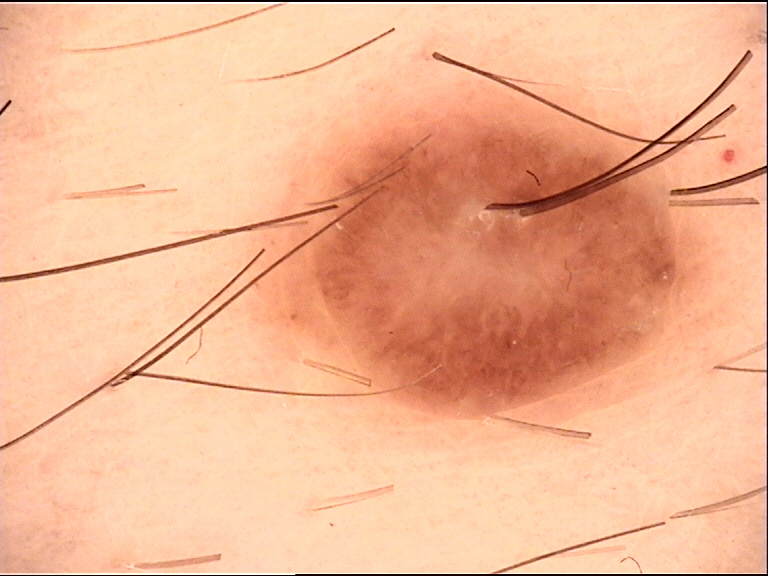• class — compound nevus (expert consensus)